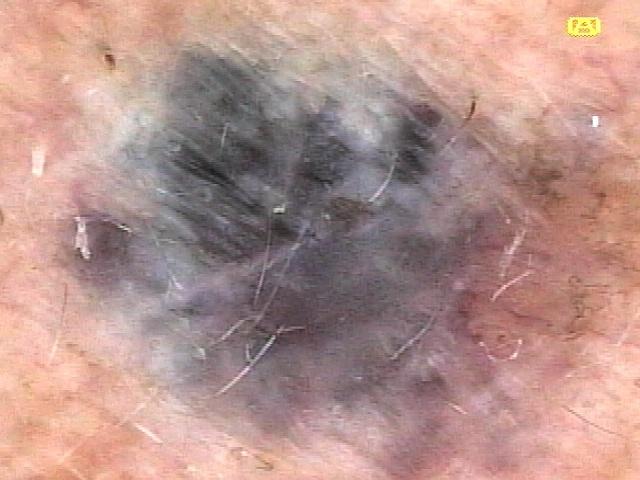Histopathologically confirmed as a basal cell carcinoma.